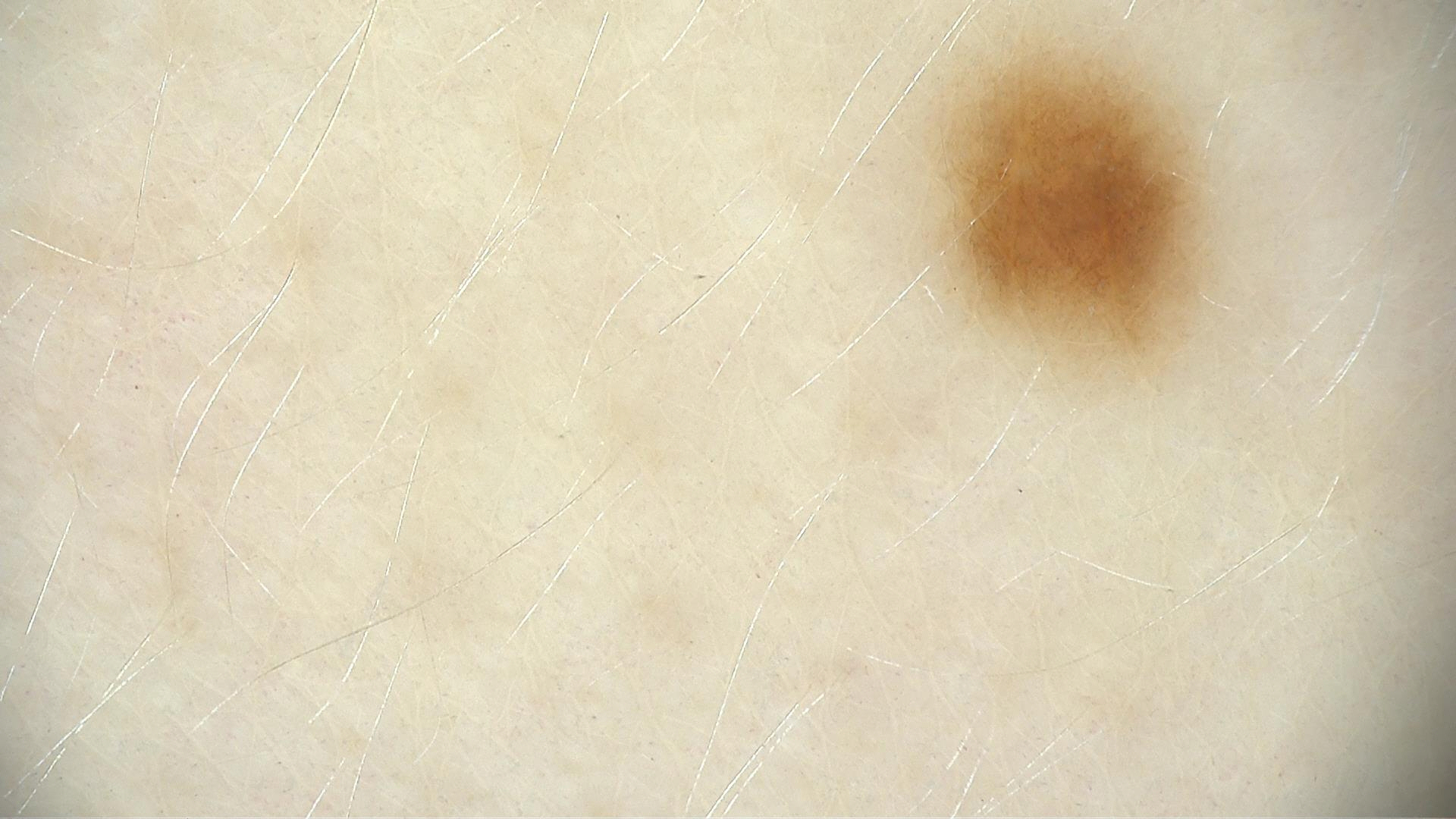Q: What kind of image is this?
A: dermoscopy
Q: What was the diagnostic impression?
A: junctional nevus (expert consensus)